Contact-polarized dermoscopy of a skin lesion:
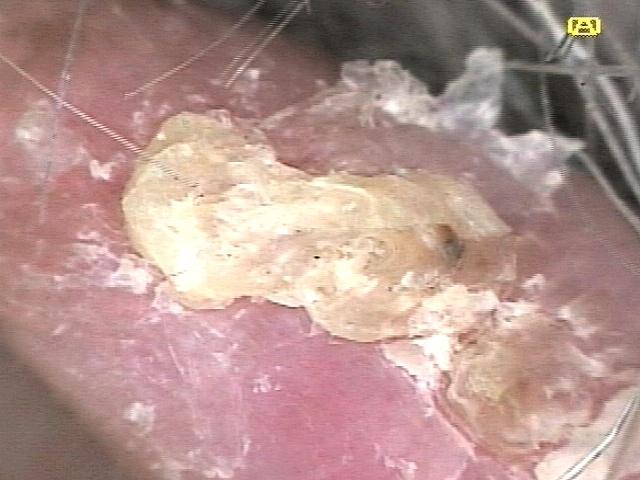The lesion is on the head or neck.
Clinically diagnosed as a solar or actinic keratosis.